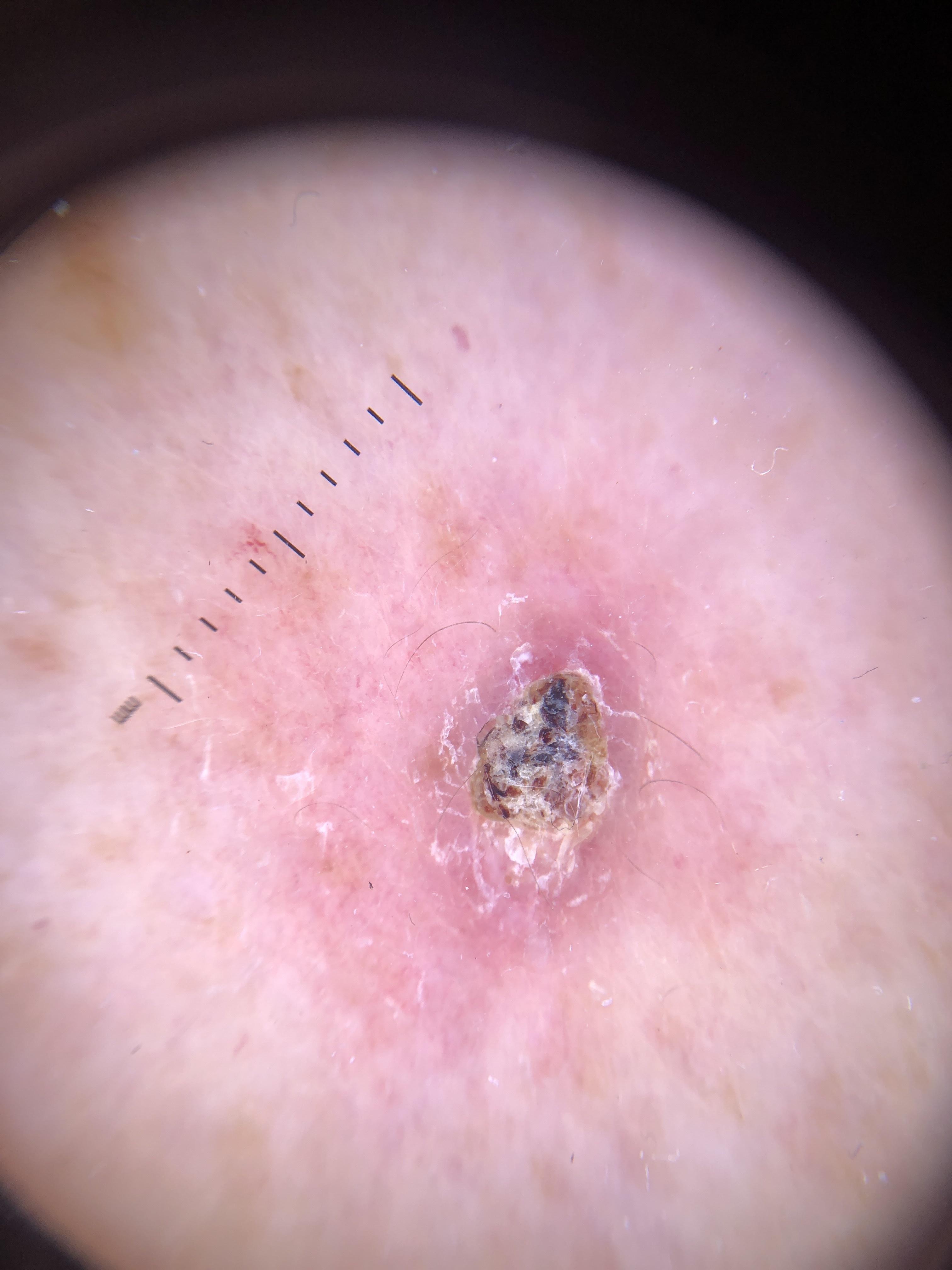<skin_lesion>
<image>dermoscopy</image>
<diagnosis>
<name>Squamous cell carcinoma</name>
<malignancy>malignant</malignancy>
<confirmation>histopathology</confirmation>
<lineage>epidermal</lineage>
</diagnosis>
</skin_lesion>